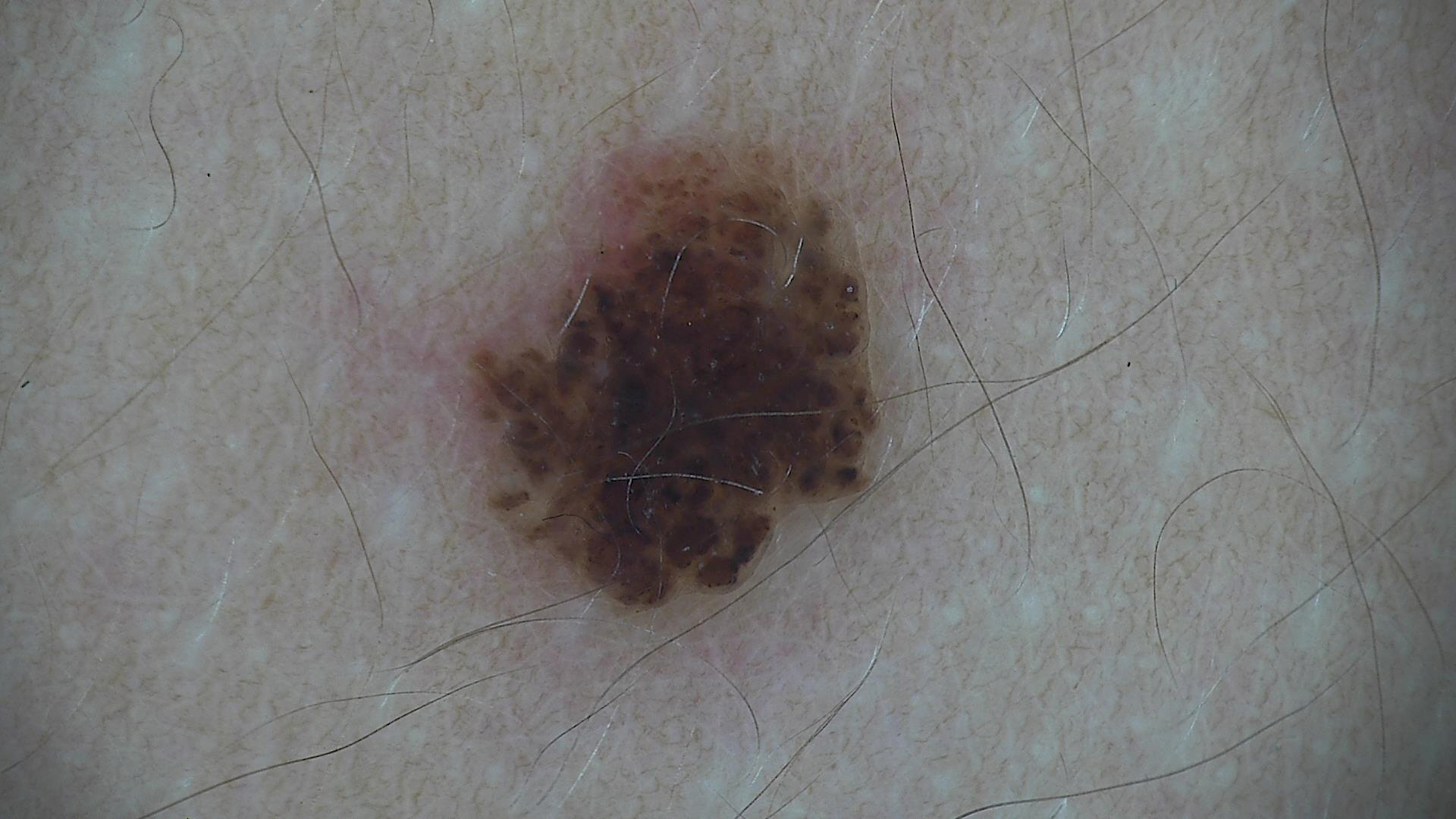assessment: compound nevus (expert consensus)